A clinical close-up of a skin lesion · a female patient 50 years old · a moderate number of moles by the patient's own estimate · the patient says their skin reddens painfully with sun exposure — 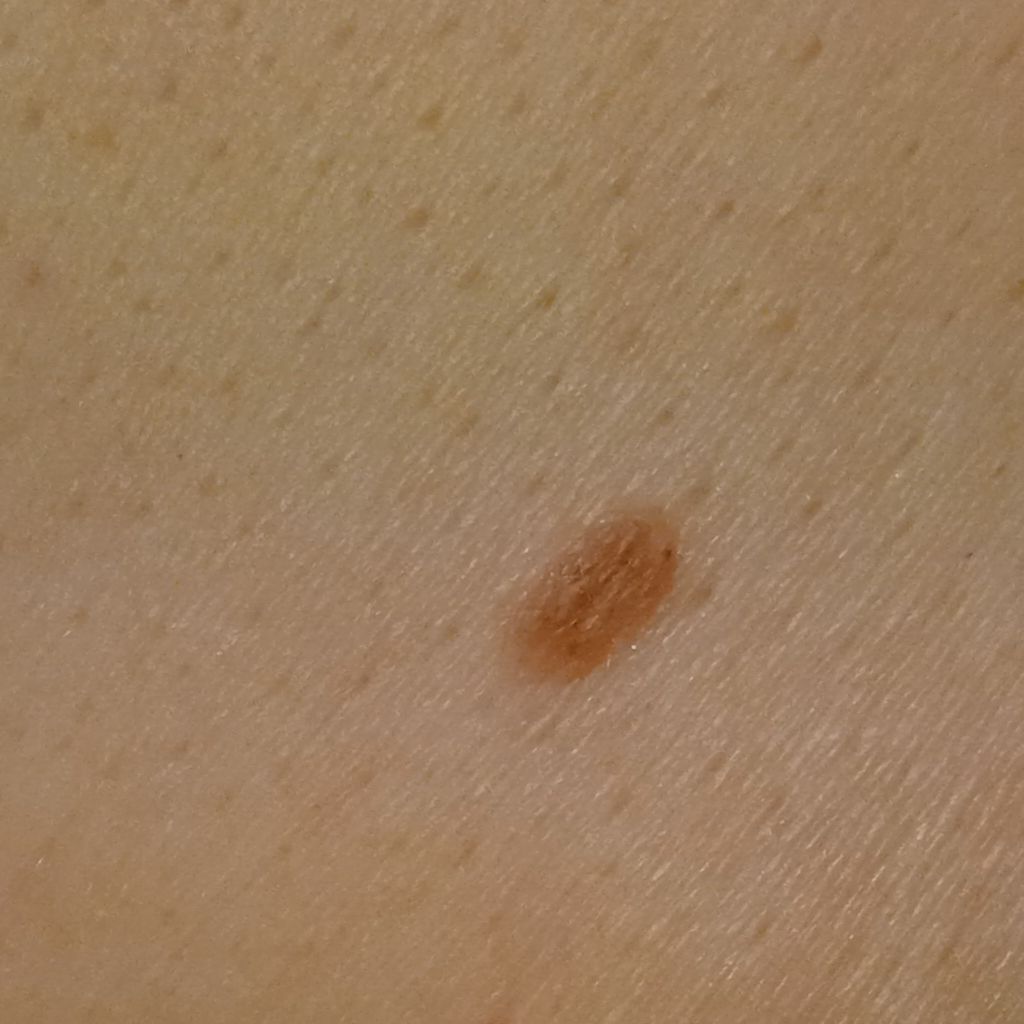The lesion involves the torso.
Measuring roughly 4.9 mm.
The consensus diagnosis for this lesion was a melanocytic nevus.